This is a close-up image · the leg is involved:
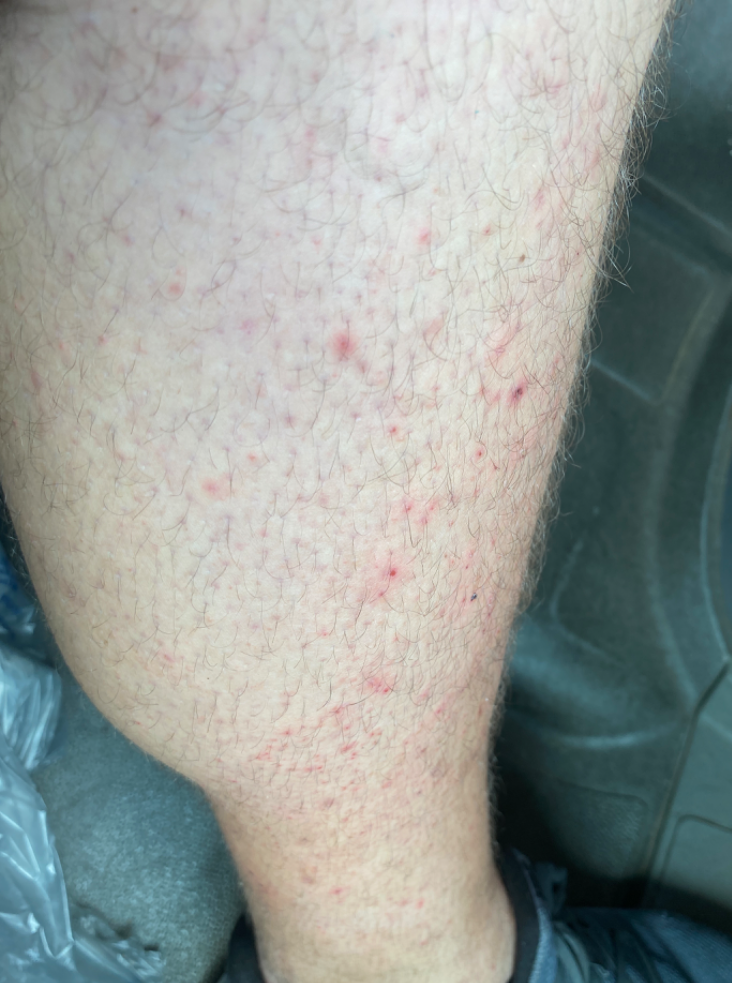Review:
The reviewing dermatologist was unable to assign a differential diagnosis from the image.
Patient information:
The lesion is associated with itching, bothersome appearance and burning. Skin tone: Fitzpatrick skin type II. The patient described the issue as acne. Reported duration is less than one week.